The photograph was taken at a distance; the contributor is 50–59, female; the patient described the issue as a rash; the affected area is the palm, leg and arm:
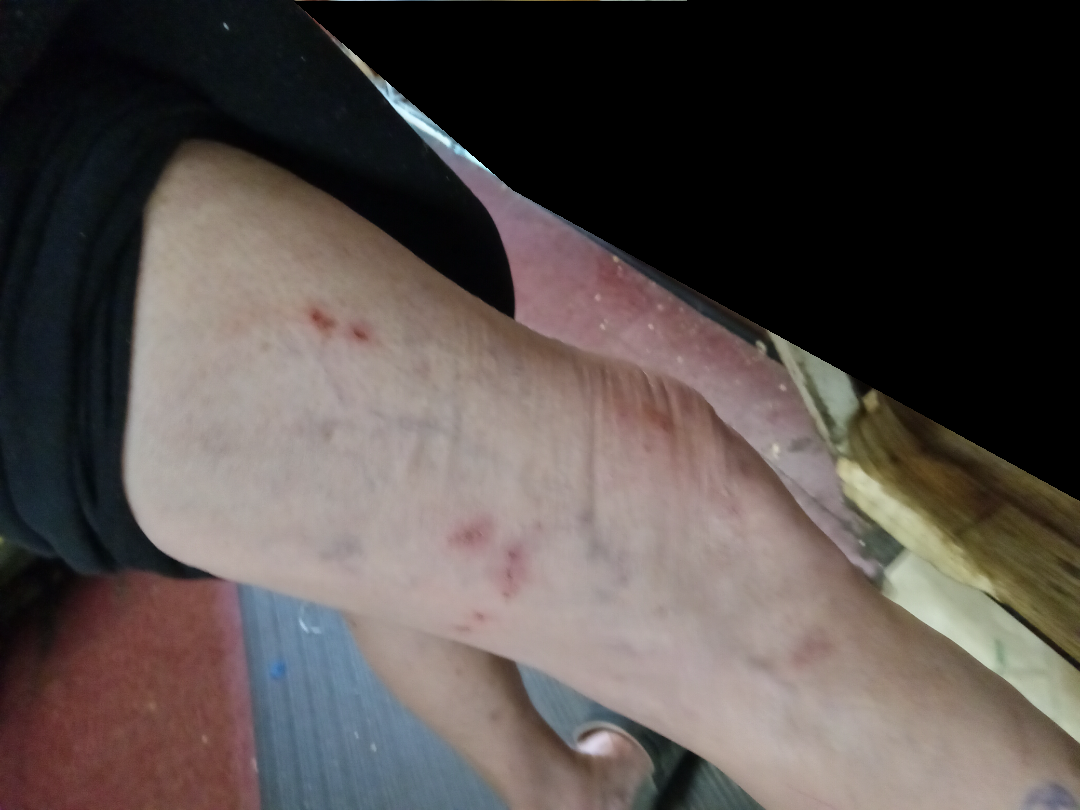Findings:
- differential diagnosis: Inflicted skin lesions and Eczema were considered with similar weight; less probable is Impetigo; a more distant consideration is Localised skin infection